A skin lesion imaged with a dermatoscope:
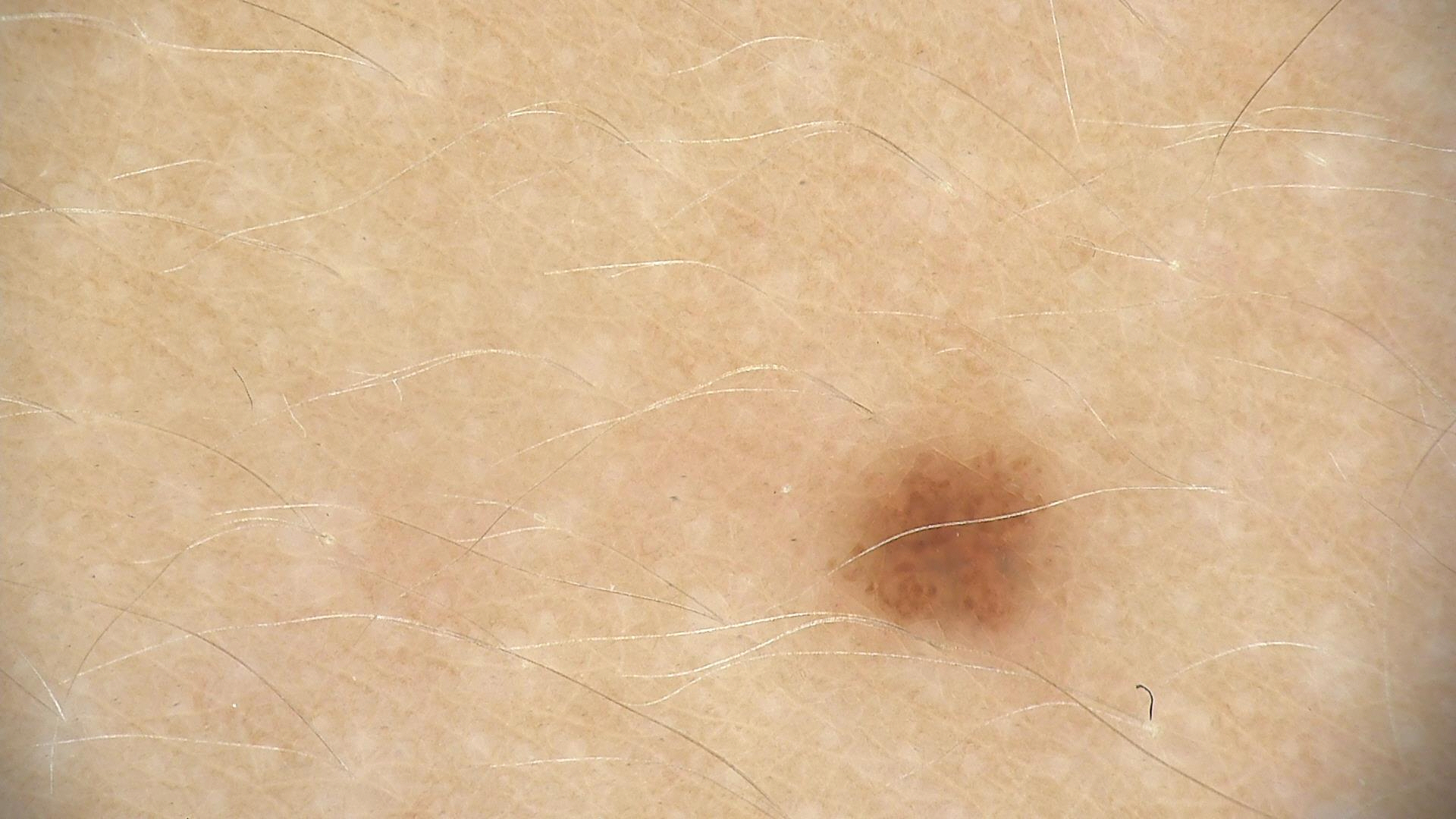Conclusion: The diagnostic label was a benign lesion — a dysplastic junctional nevus.